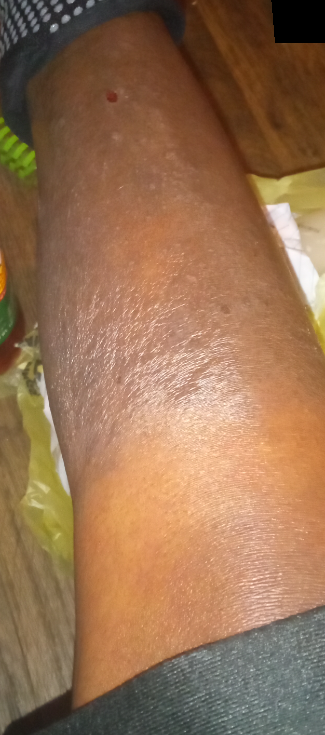Case summary:
- symptom duration: more than one year
- reported symptoms: itching, bothersome appearance, burning and darkening
- framing: close-up
- body site: top or side of the foot and leg
- self-categorized as: a rash
- dermatologist impression: Stasis Dermatitis (weight 0.33); Eczema (weight 0.33); Contact dermatitis, NOS (weight 0.33)